A dermoscopic image of a skin lesion: 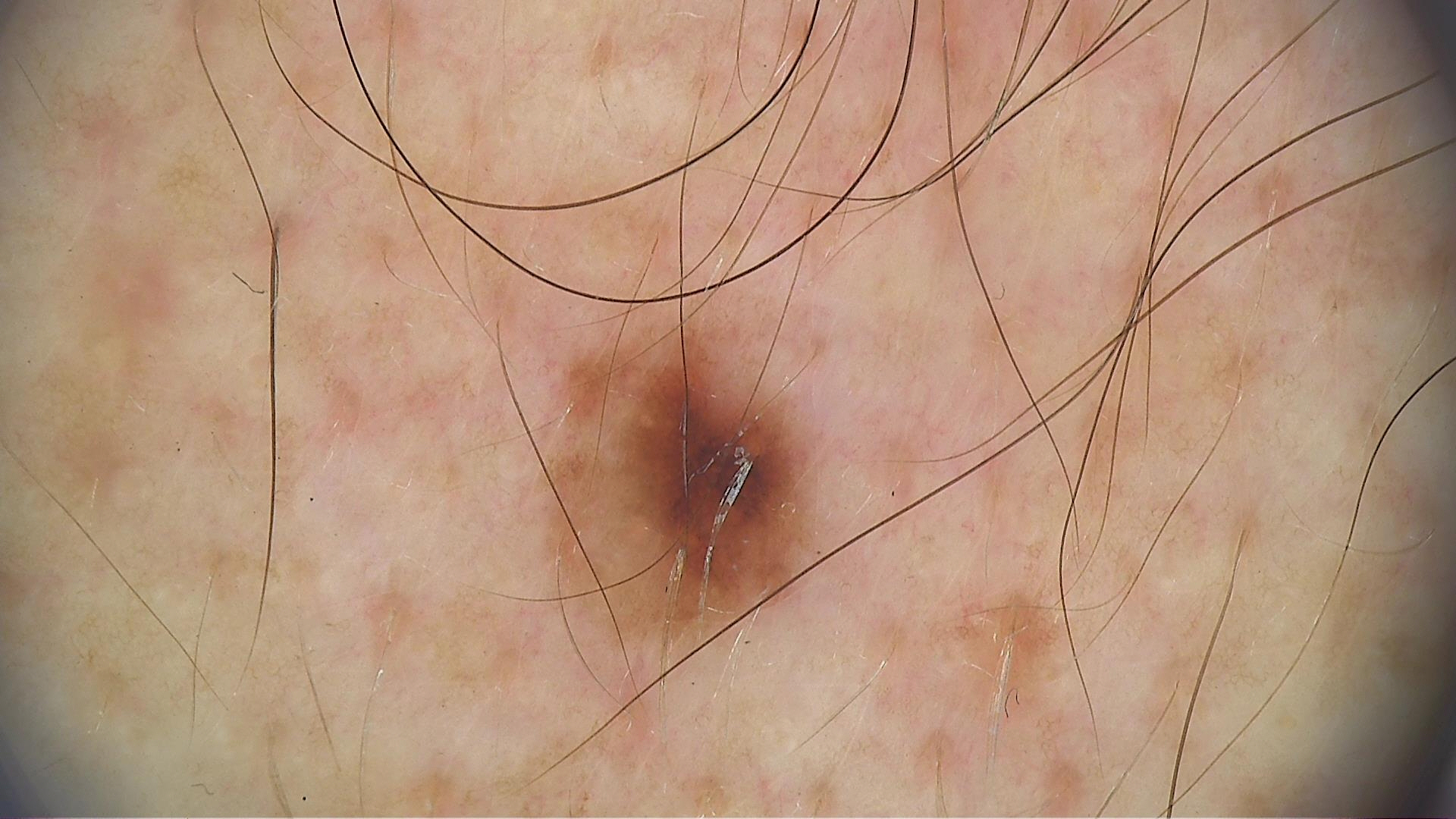label: dysplastic junctional nevus (expert consensus).